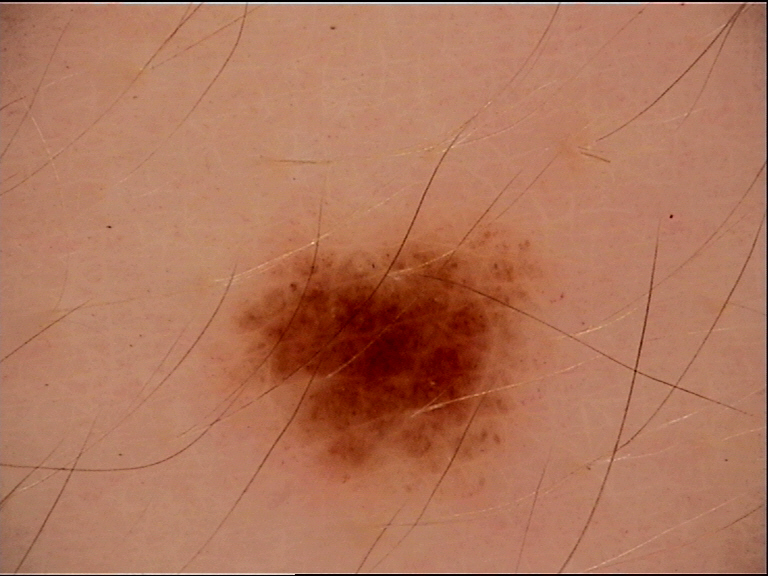* image type — dermoscopy
* diagnosis — dysplastic junctional nevus (expert consensus)